An image taken at an angle: 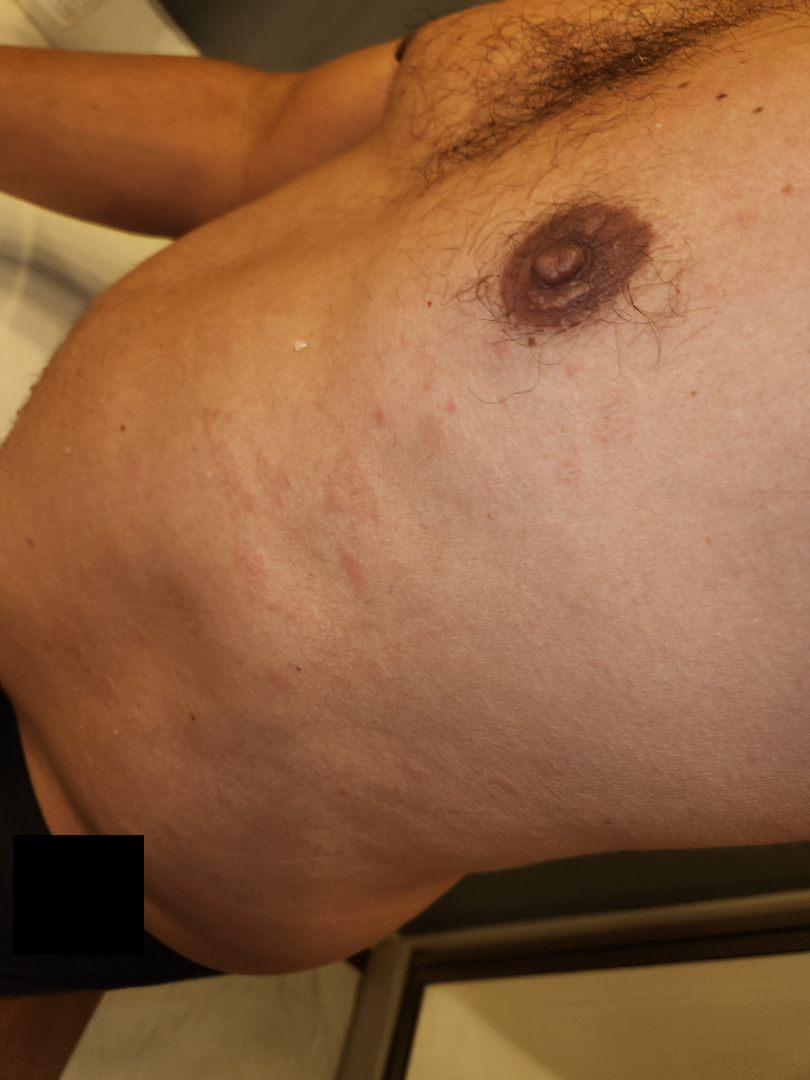| key | value |
|---|---|
| differential | Pityriasis rosea (0.67); Syphilis (0.33) |